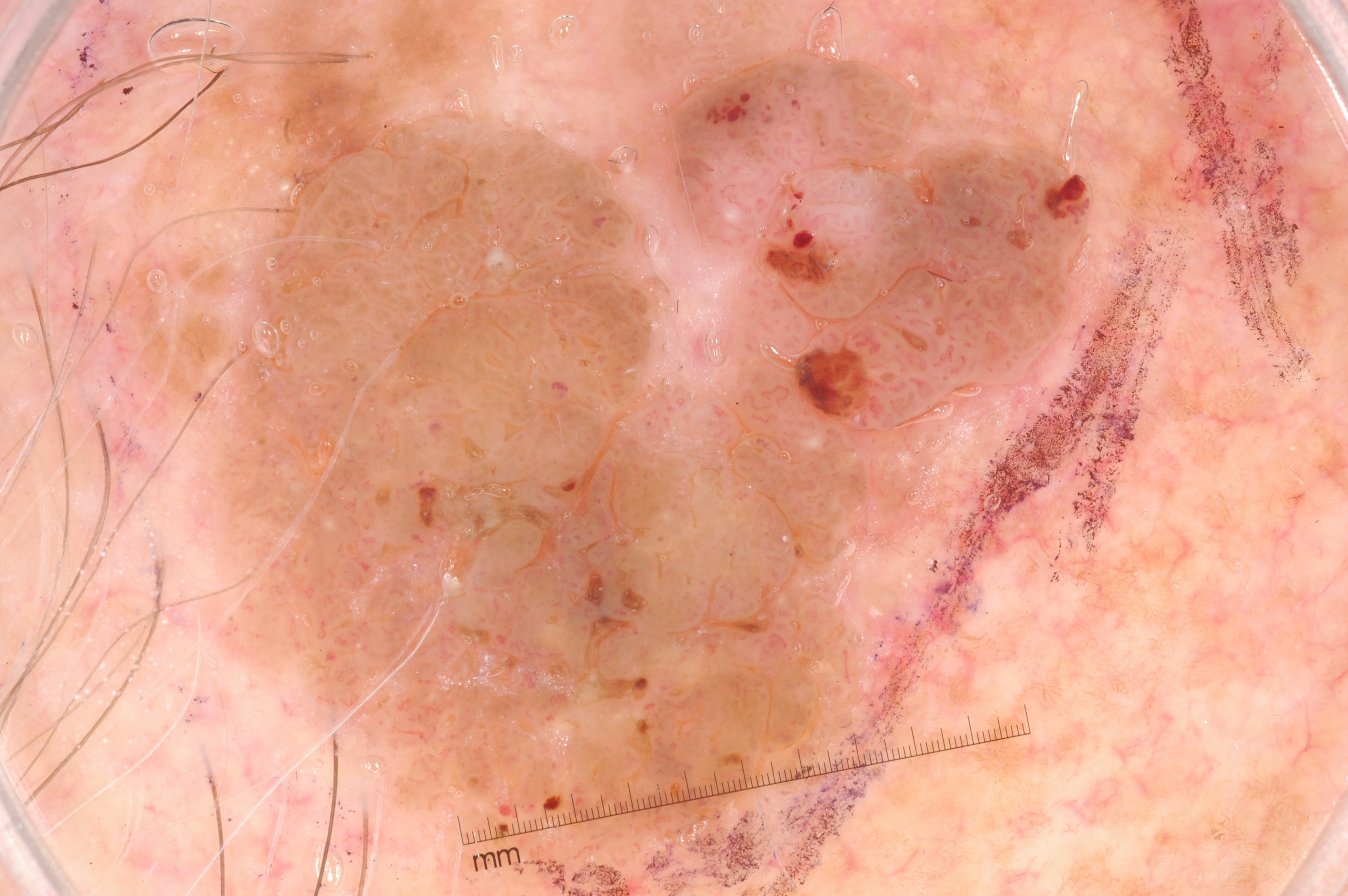Summary:
A dermoscopic image of a skin lesion. With coordinates (x1, y1, x2, y2), the lesion spans <bbox>106, 0, 1126, 889</bbox>.
Impression:
Consistent with a seborrheic keratosis.